The subject is a female aged 40–49; the lesion involves the arm; a close-up photograph.
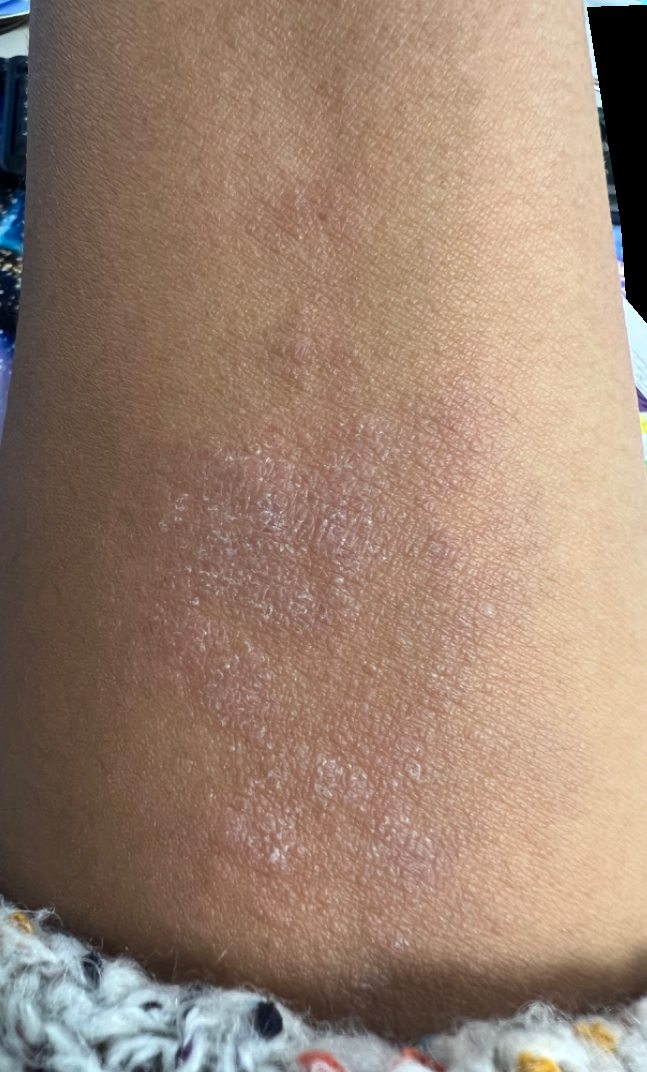Impression: The reviewing clinician's impression was: Eczema (leading); Psoriasis (considered).